A male patient, roughly 45 years of age · dermoscopy of a skin lesion: 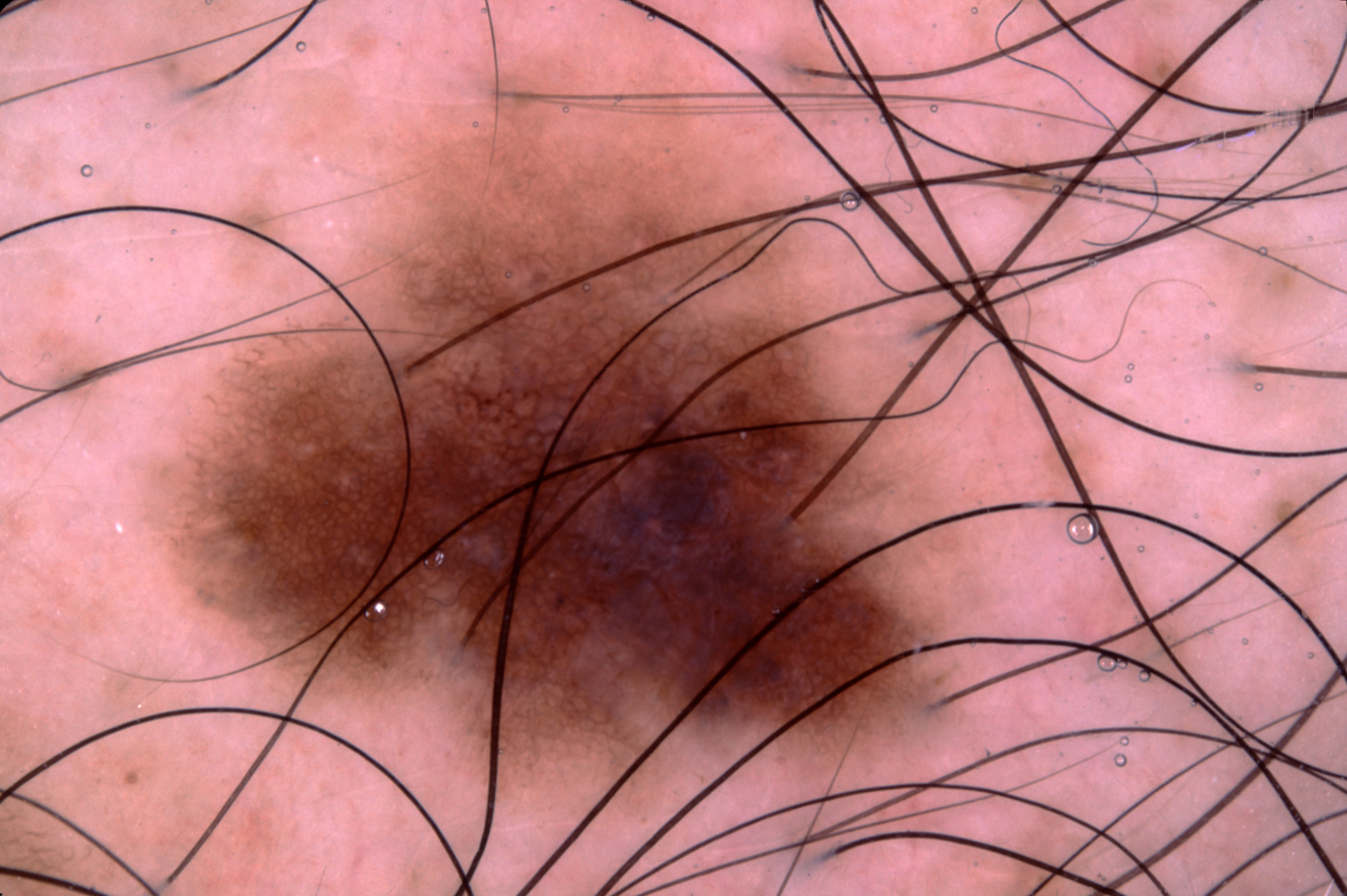  lesion_location:
    bbox_xyxy:
      - 129
      - 46
      - 979
      - 841
  dermoscopic_features:
    present:
      - pigment network
    absent:
      - negative network
      - streaks
      - milia-like cysts
  diagnosis:
    name: melanocytic nevus
    malignancy: benign
    lineage: melanocytic
    provenance: clinical